An image taken at a distance · reported duration is less than one week · the leg, arm and head or neck are involved · the patient considered this a rash · the patient is a female aged 70–79 · no associated lesion symptoms were reported:
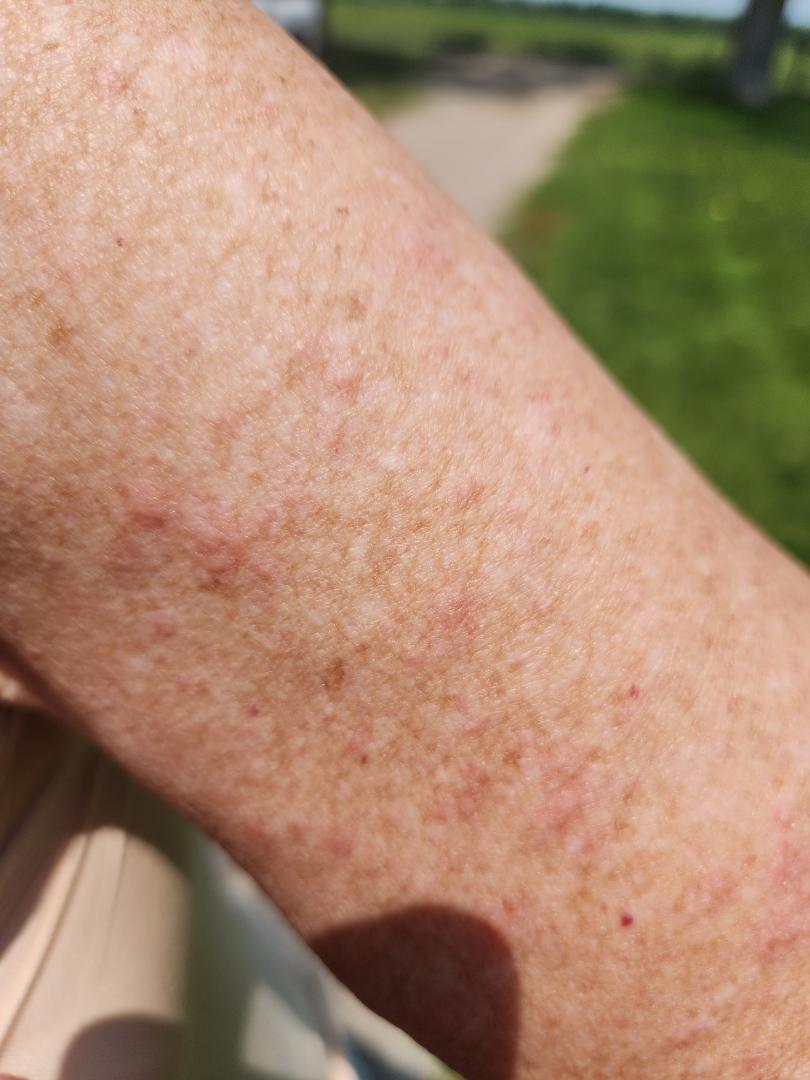assessment = unable to determine